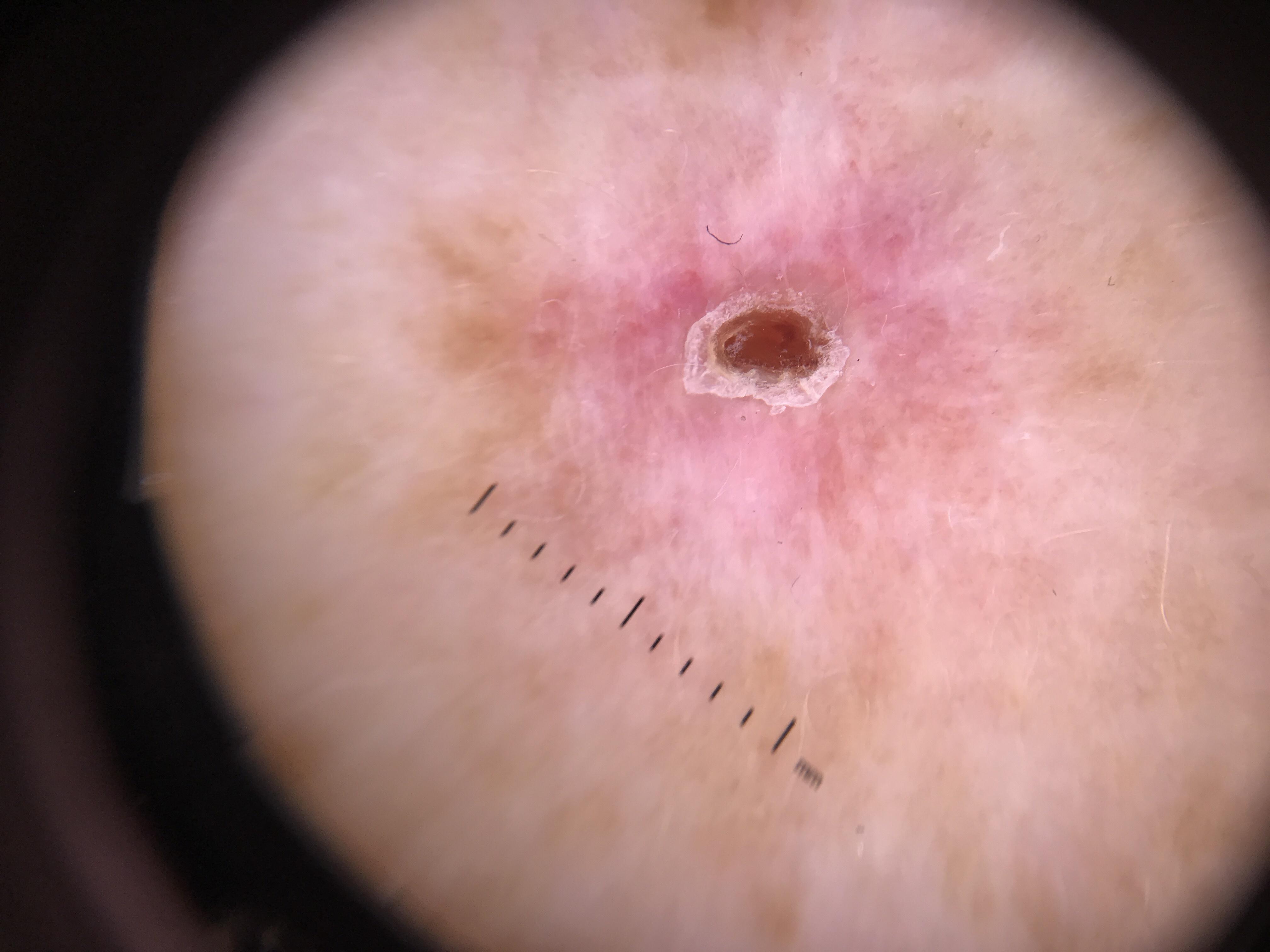location: an upper extremity
pathology: Melanoma (biopsy-proven)